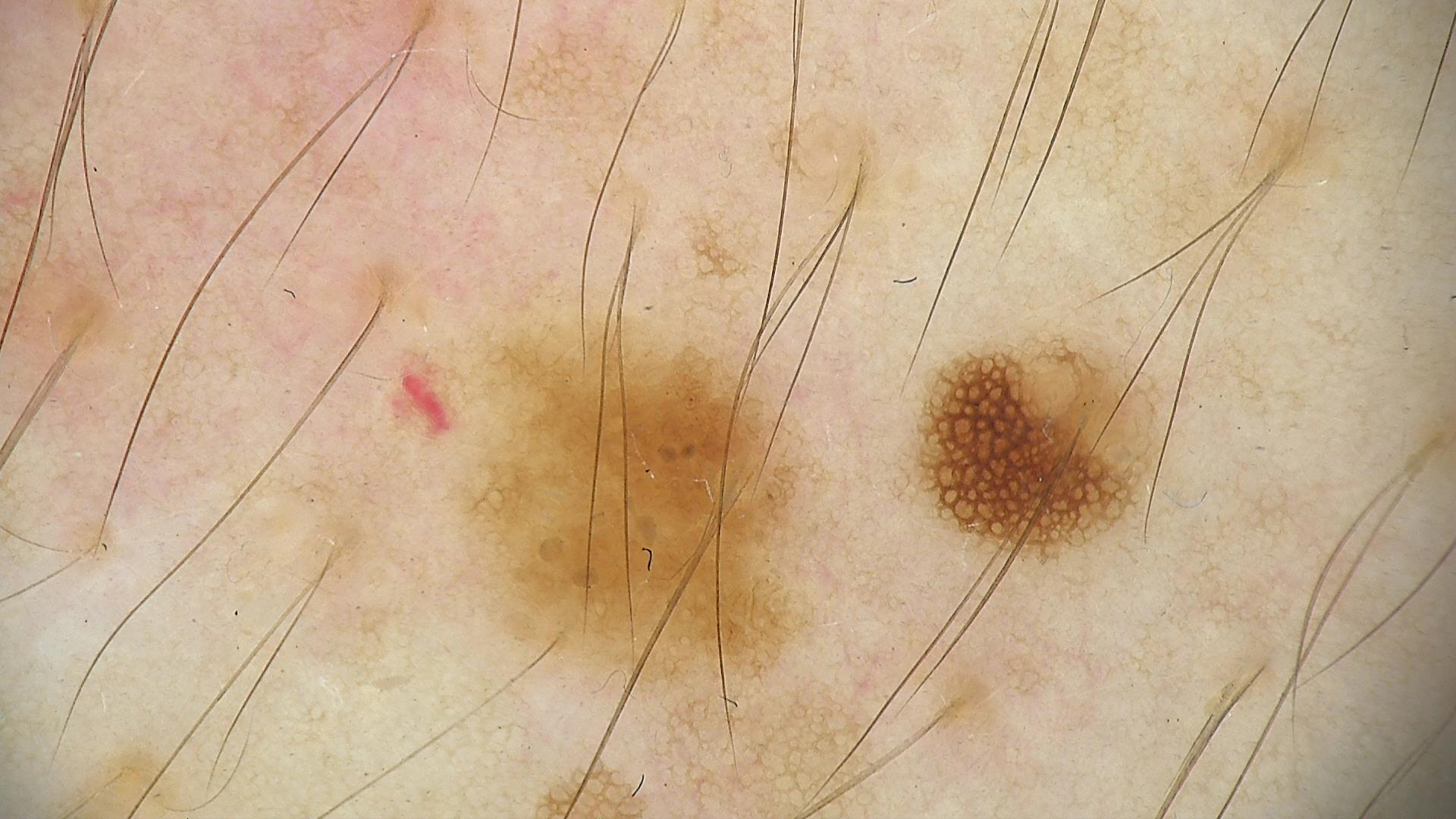A skin lesion imaged with a dermatoscope. Diagnosed as a benign lesion — a dysplastic junctional nevus.